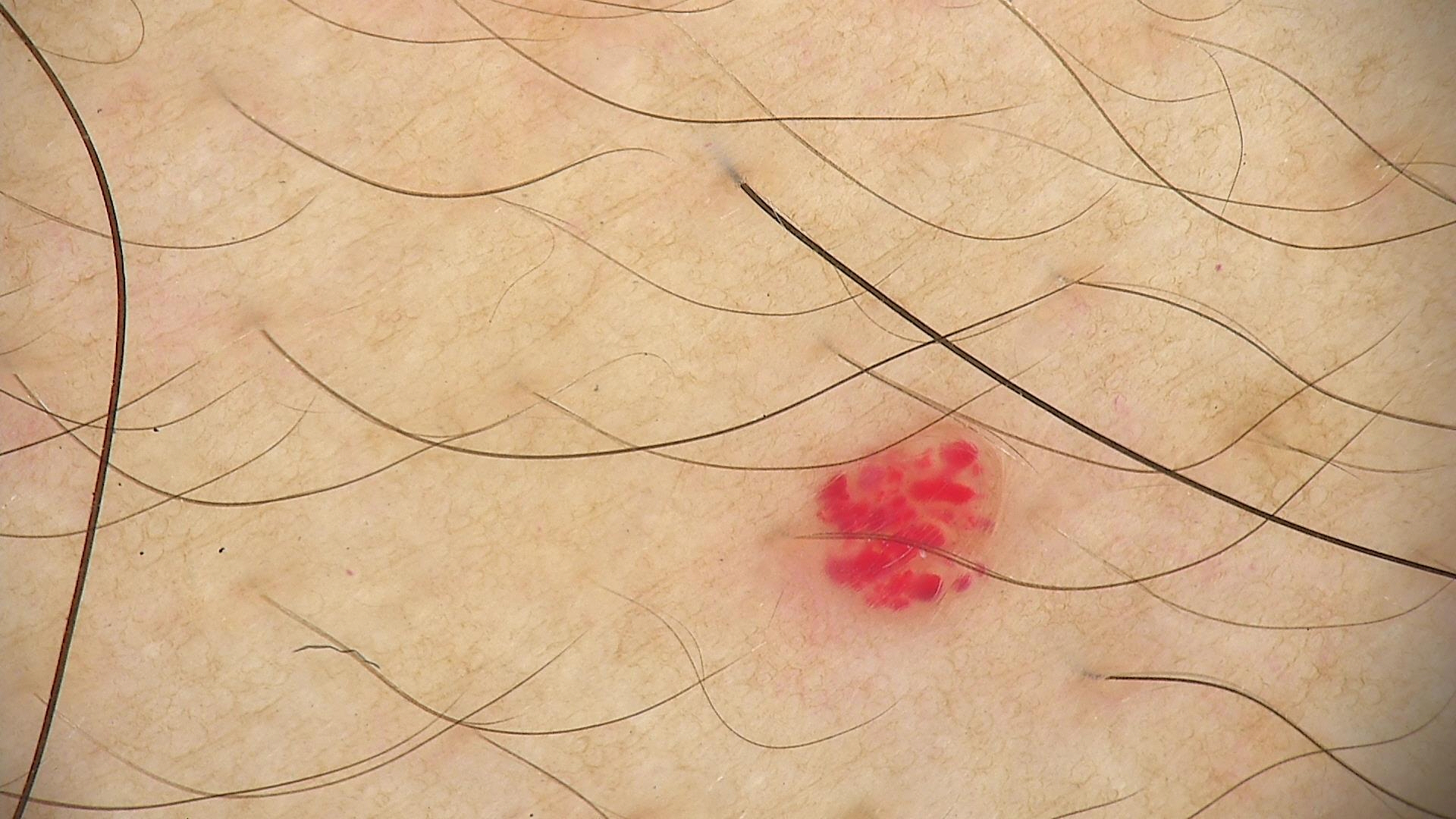lesion type: vascular
label: hemangioma (expert consensus)